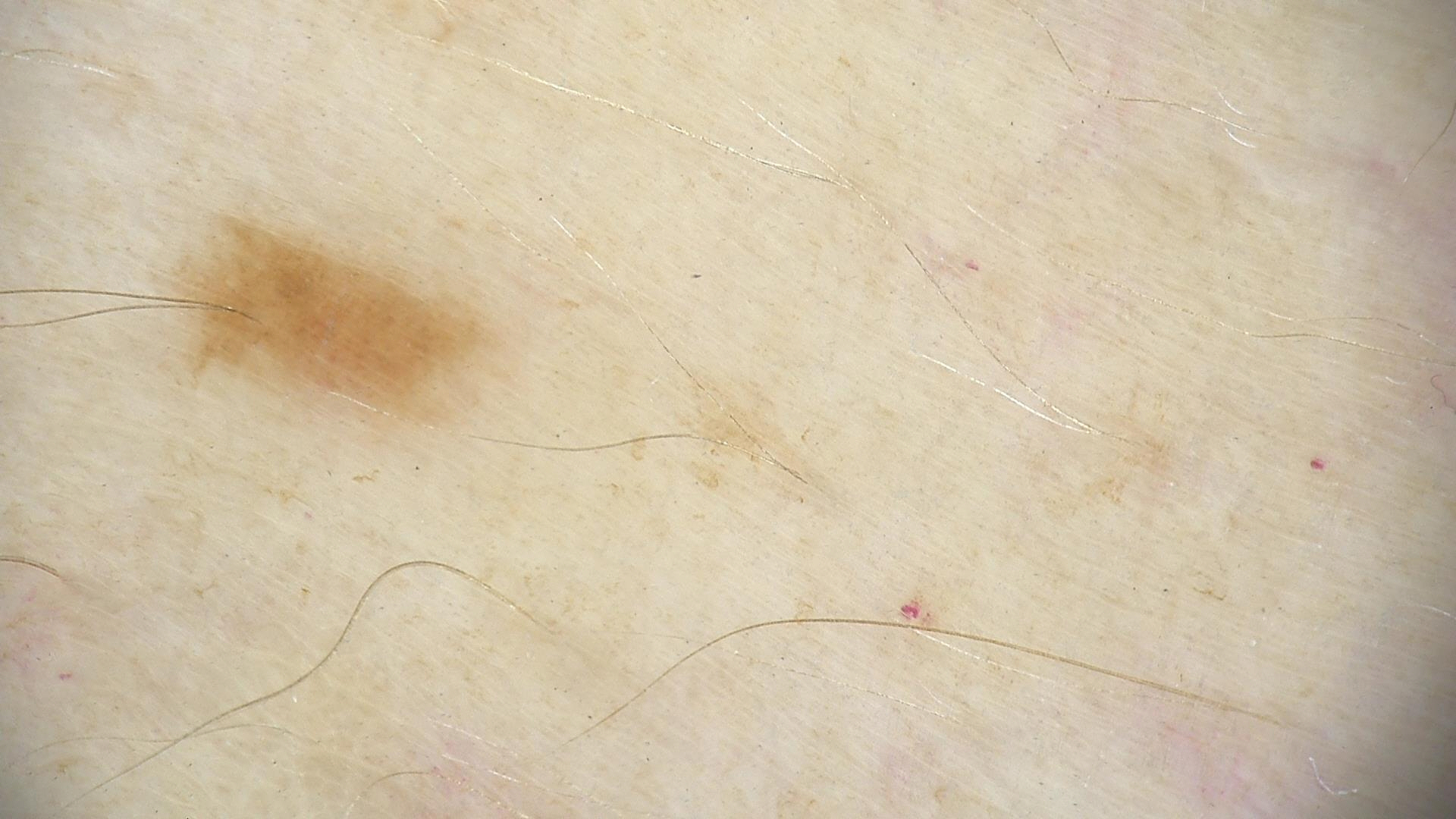Impression:
Diagnosed as a banal lesion — a junctional nevus.